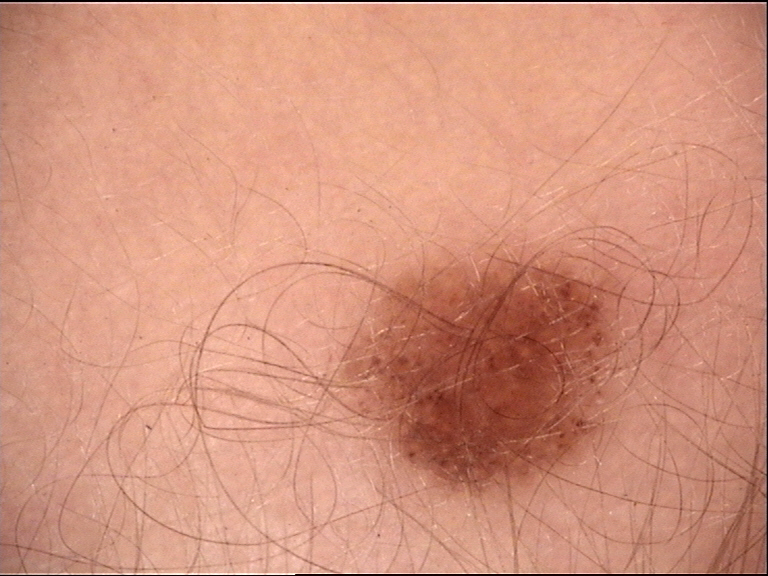Impression:
Diagnosed as a junctional nevus.